The lesion involves the leg and arm. Close-up view — 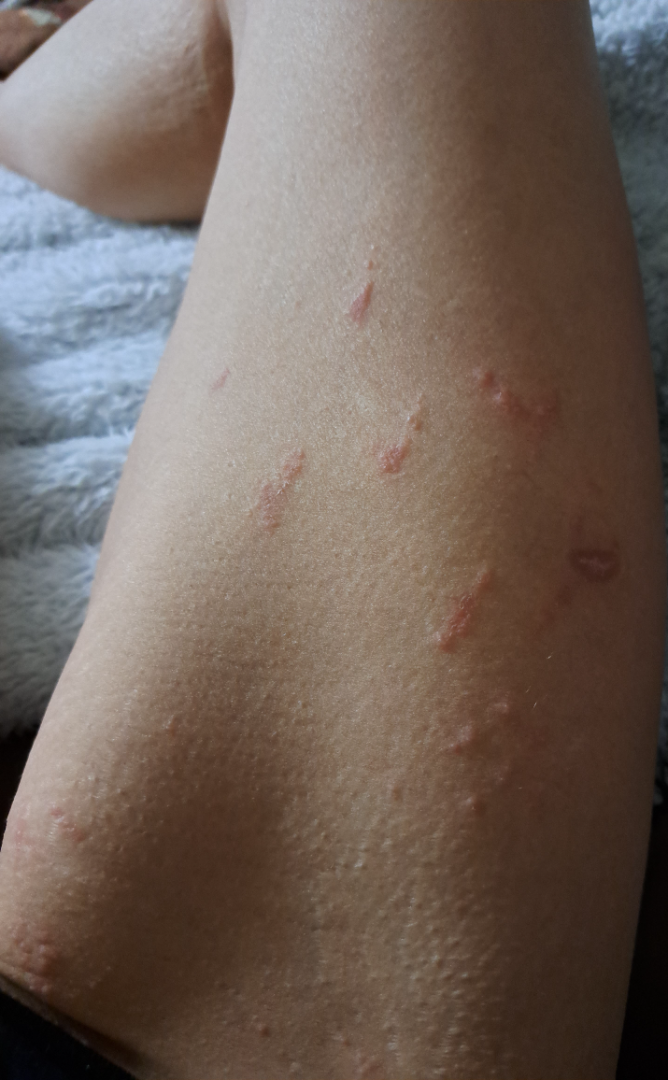Assessment: The case was indeterminate on photographic review. Clinical context: Symptoms reported: itching. The contributor reports the lesion is raised or bumpy and fluid-filled. The patient considered this a rash. Present for less than one week.